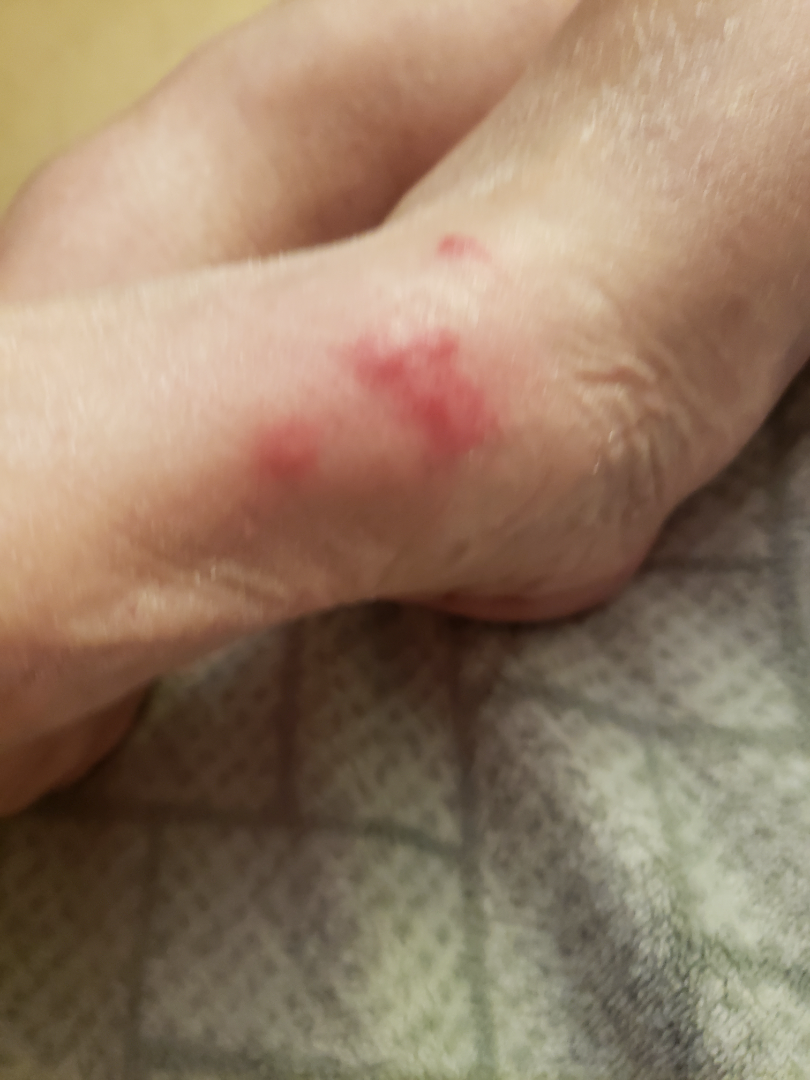The case was difficult to assess from the available photograph. The affected area is the top or side of the foot. This is a close-up image. The patient is female. The patient indicates the lesion is raised or bumpy. The patient indicates the condition has been present for about one day. The patient indicates itching, burning and pain.